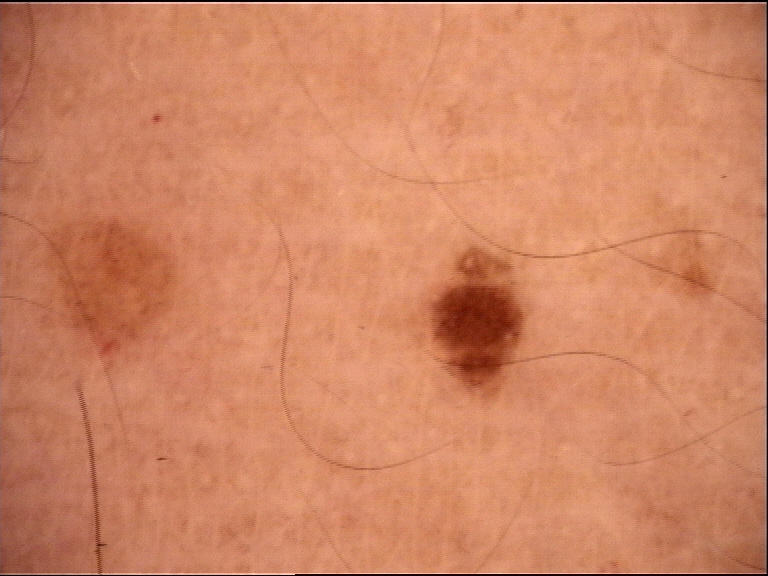{"image": "dermatoscopy", "diagnosis": {"name": "junctional nevus", "code": "jb", "malignancy": "benign", "super_class": "melanocytic", "confirmation": "expert consensus"}}